A dermoscopy image of a single skin lesion:
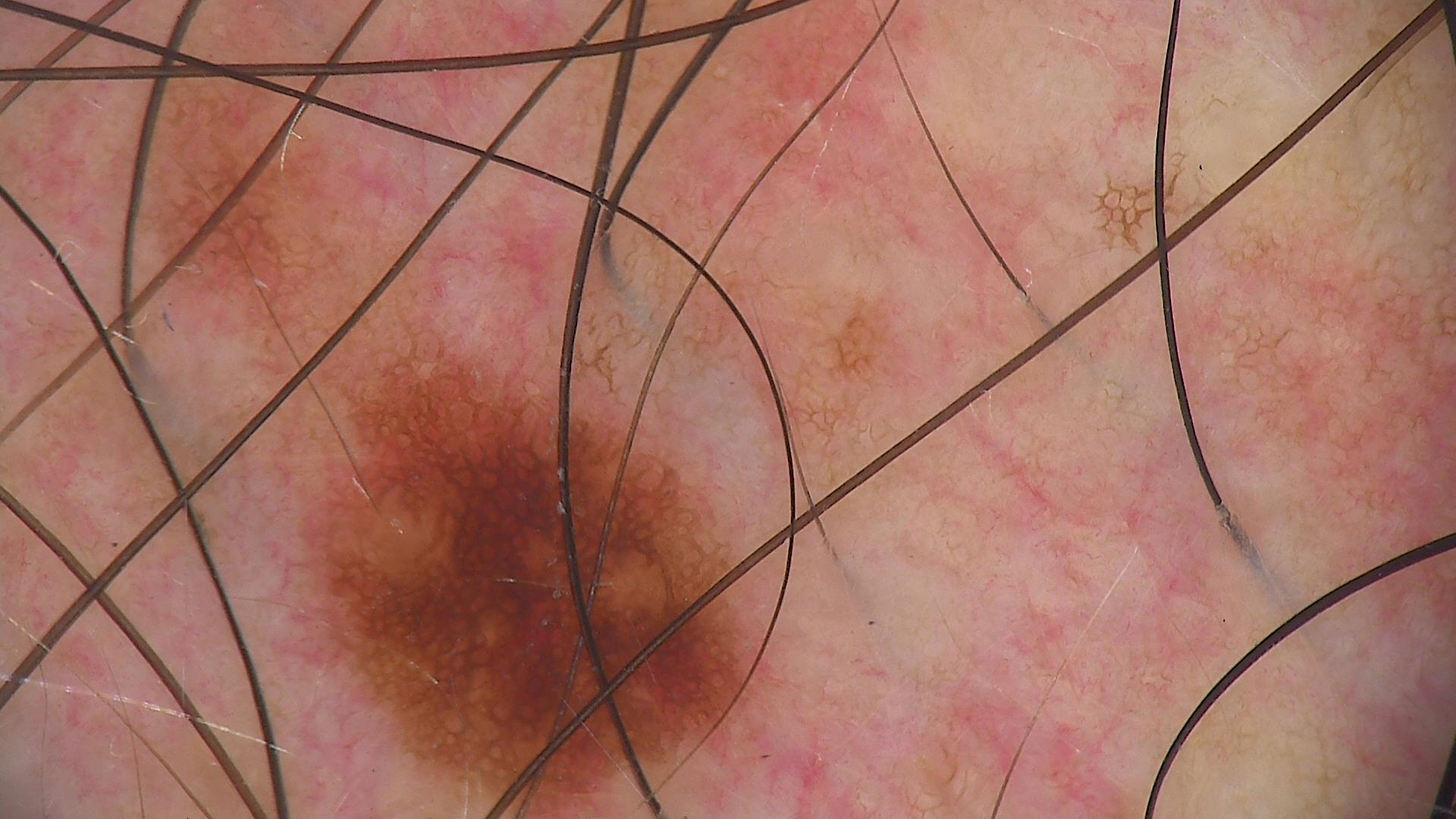Classified as a dysplastic junctional nevus.